This image was taken at a distance · the lesion involves the back of the torso, back of the hand, leg, front of the torso, top or side of the foot, arm, sole of the foot, head or neck and palm: 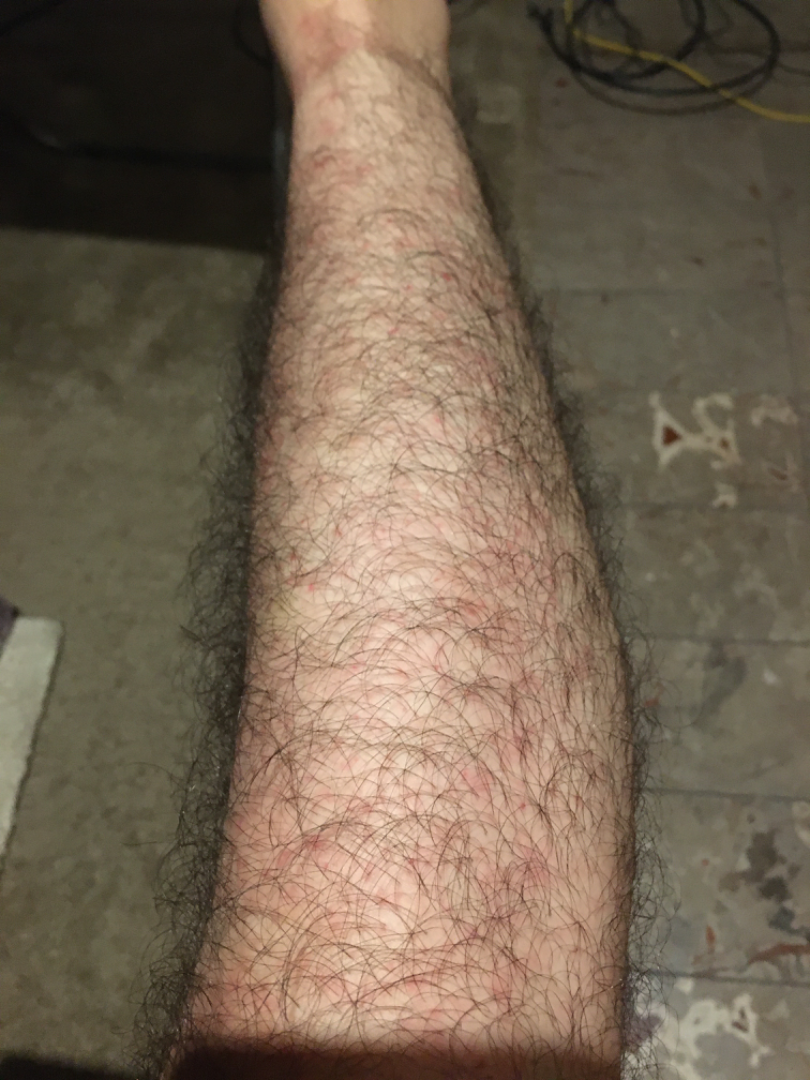– diagnostic considerations — Folliculitis, Eczema and Allergic Contact Dermatitis were considered with similar weight